A dermoscopic close-up of a skin lesion · a male patient, approximately 65 years of age:
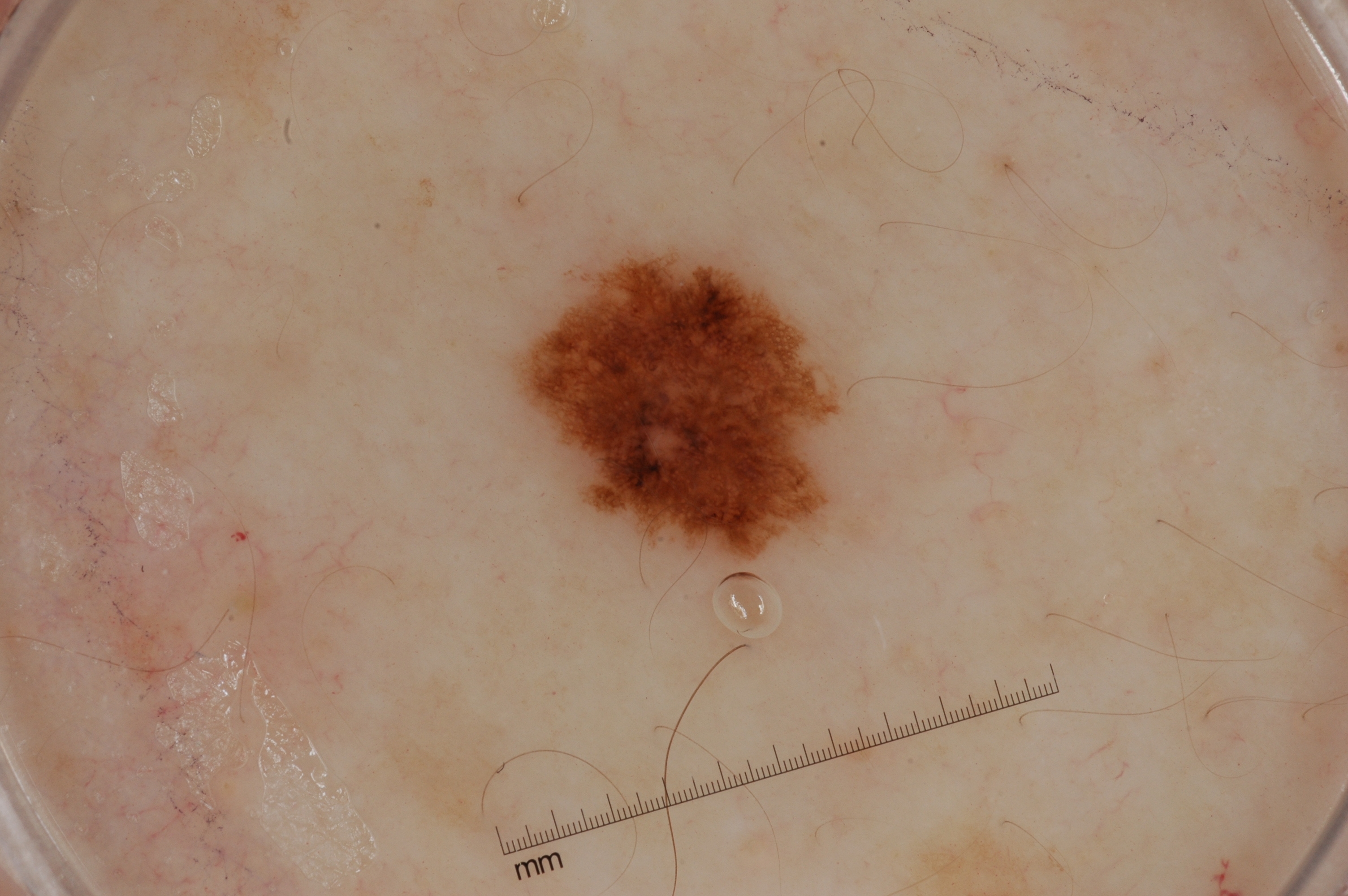The lesion is small relative to the field of view. Dermoscopically, the lesion shows pigment network. In (x1, y1, x2, y2) order, the lesion occupies the region 516/252/842/567. Clinically diagnosed as a melanocytic nevus.